A dermoscopic photograph of a skin lesion:
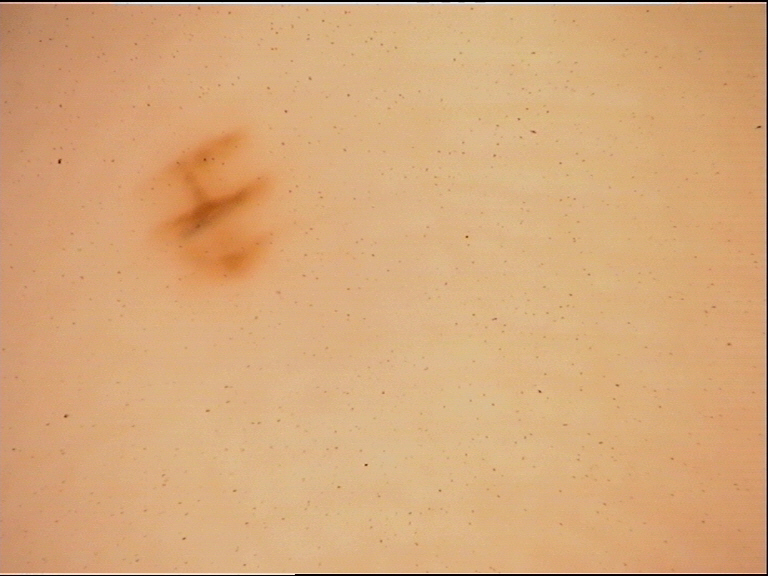{
  "diagnosis": {
    "name": "acral dysplastic junctional nevus",
    "code": "ajd",
    "malignancy": "benign",
    "super_class": "melanocytic",
    "confirmation": "expert consensus"
  }
}